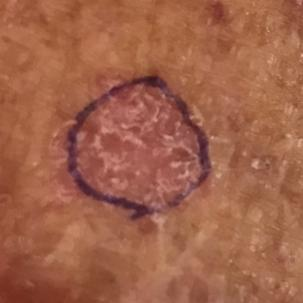Conclusion:
The diagnostic impression was an actinic keratosis.